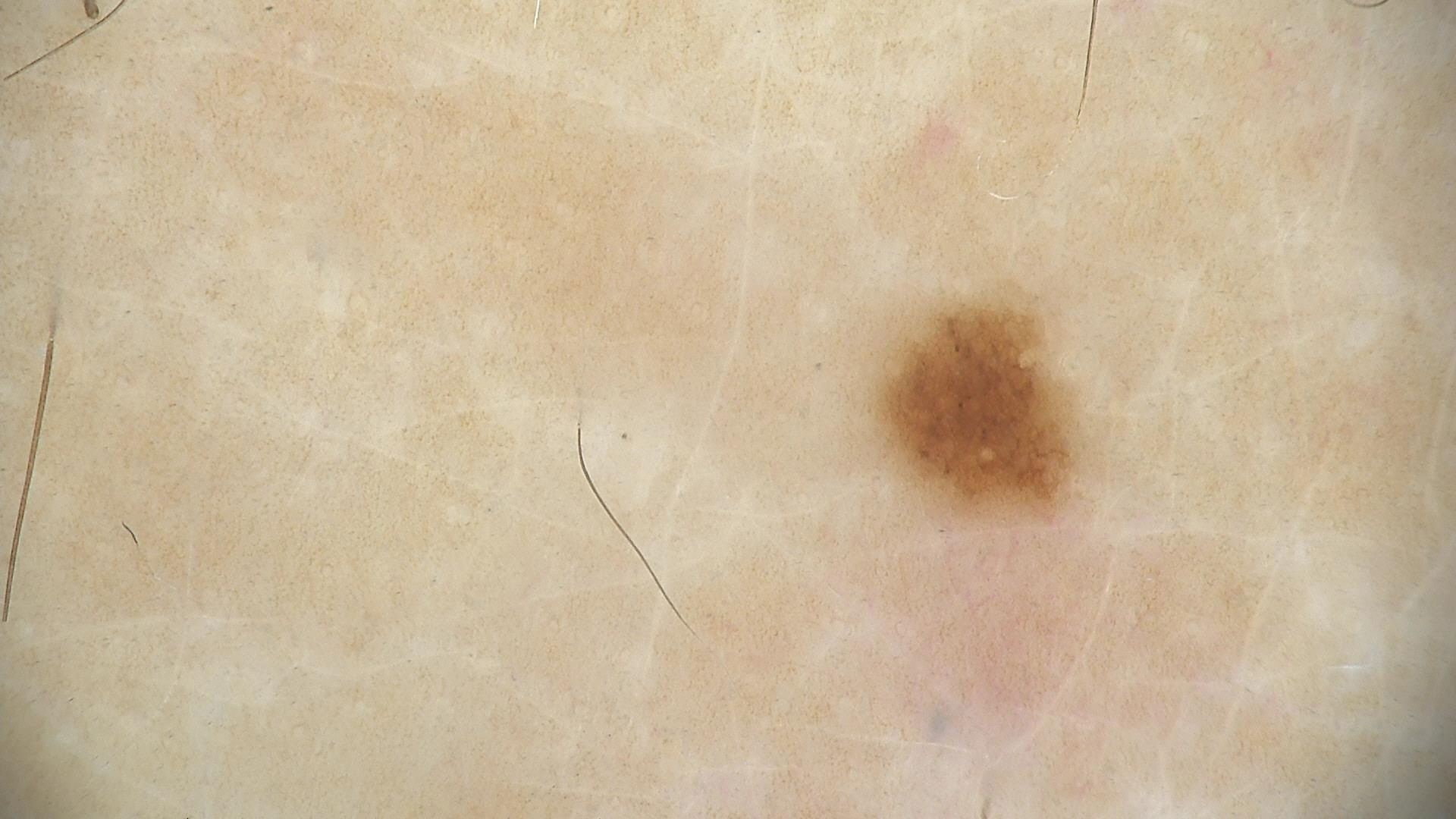<lesion>
<diagnosis>
<name>dysplastic junctional nevus</name>
<code>jd</code>
<malignancy>benign</malignancy>
<super_class>melanocytic</super_class>
<confirmation>expert consensus</confirmation>
</diagnosis>
</lesion>